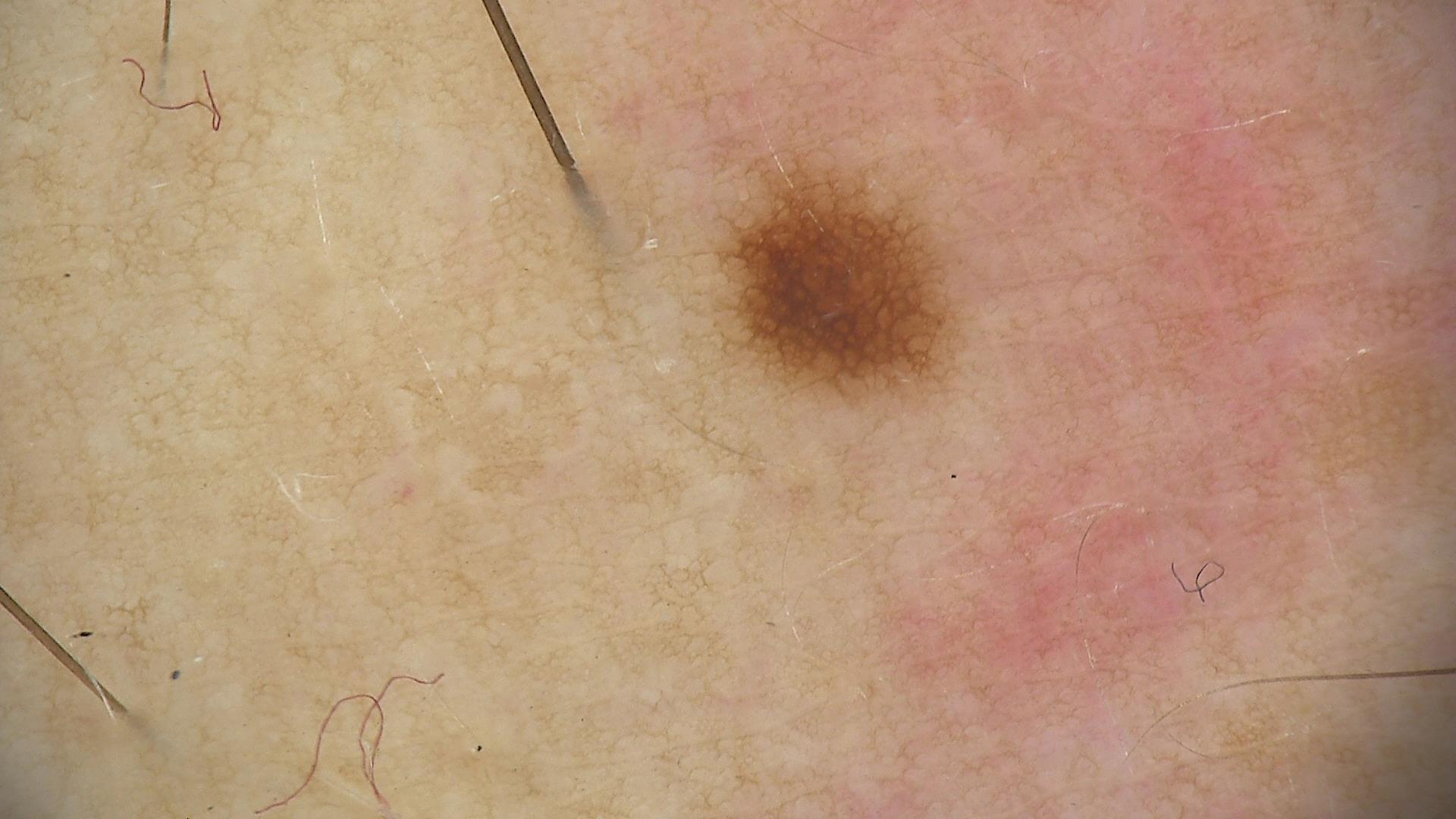imaging: dermatoscopy
assessment: dysplastic junctional nevus (expert consensus)